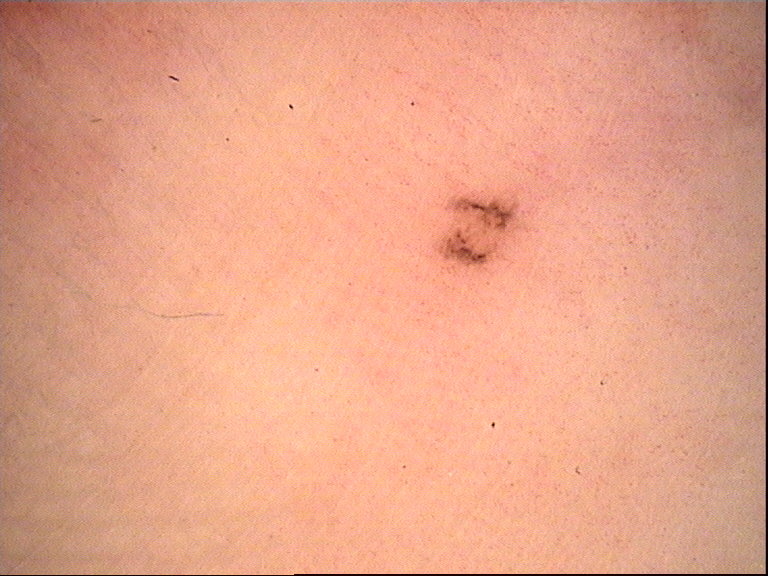Q: What is the imaging modality?
A: dermatoscopy
Q: What is this lesion?
A: acral dysplastic junctional nevus (expert consensus)